A dermoscopy image of a single skin lesion: 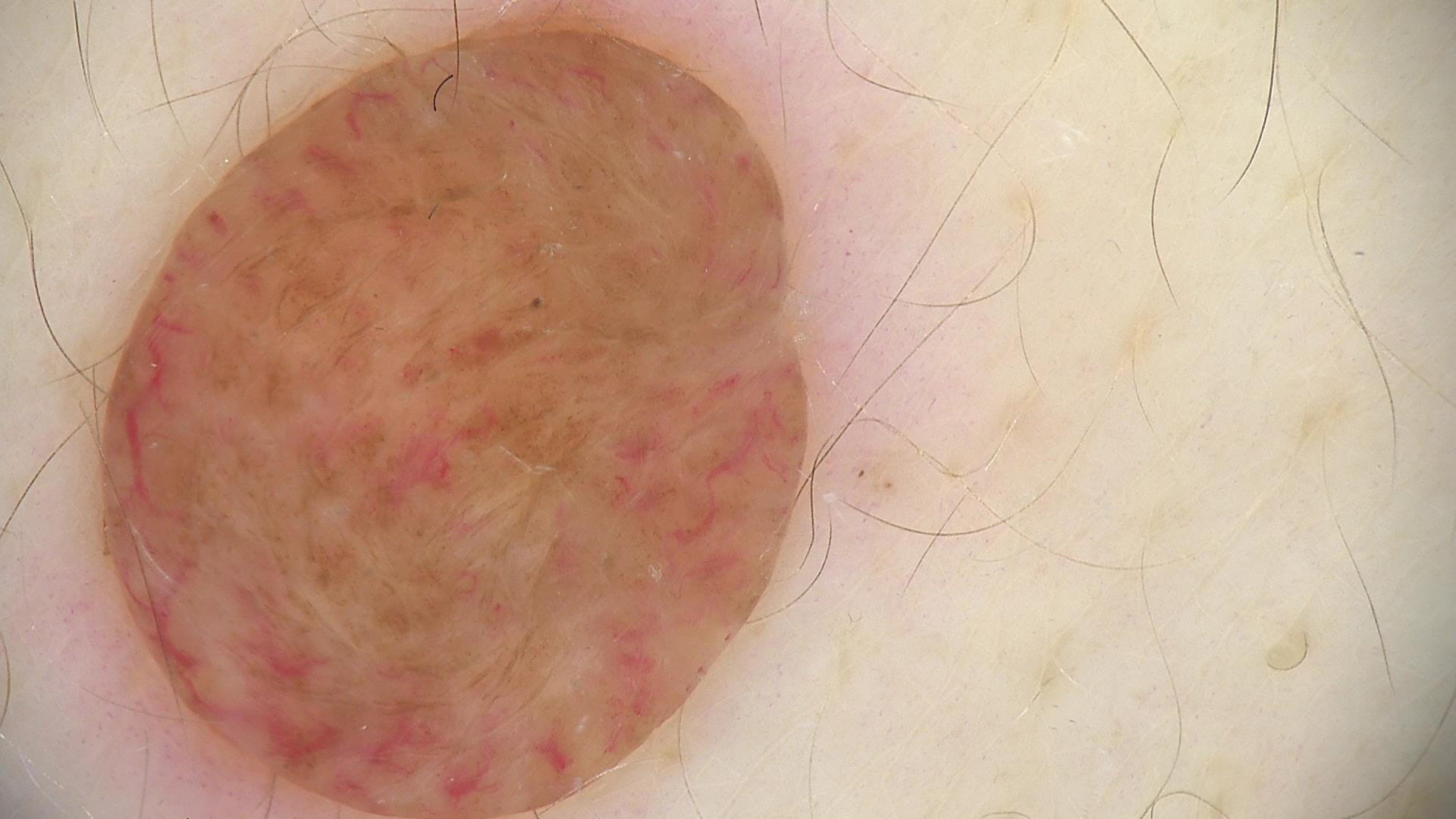The architecture is that of a banal lesion. Classified as a dermal nevus.